Close-up view:
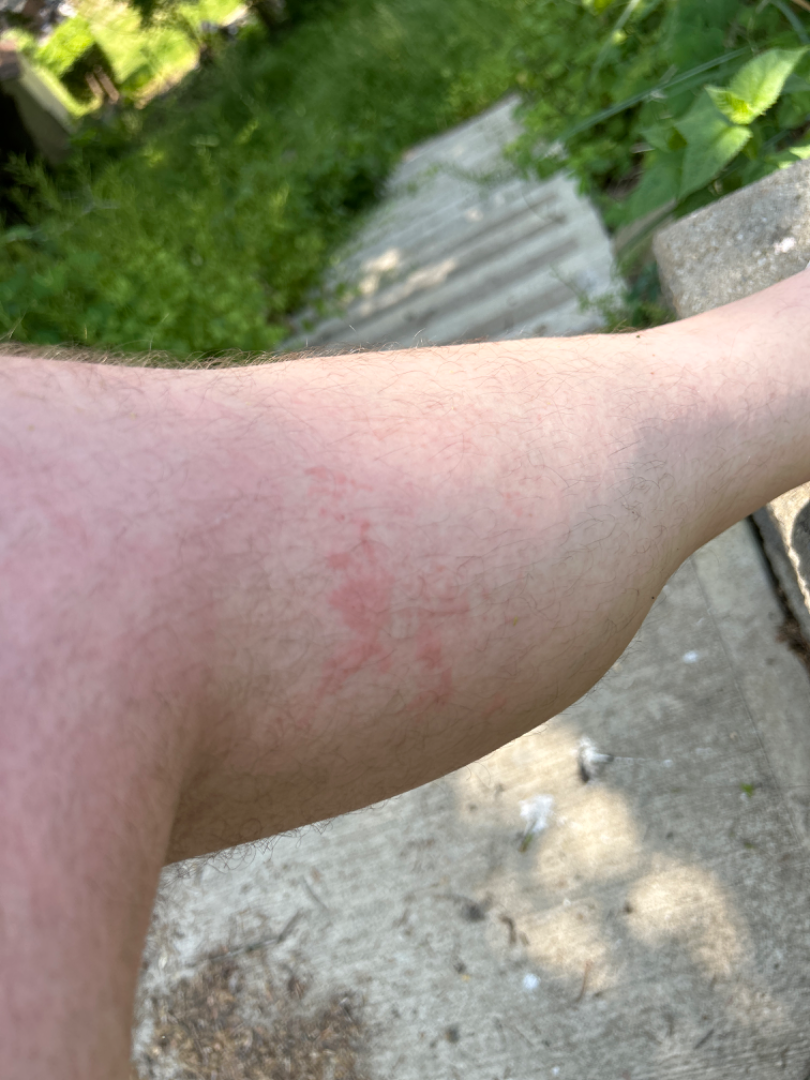Q: Could the case be diagnosed?
A: ungradable on photographic review